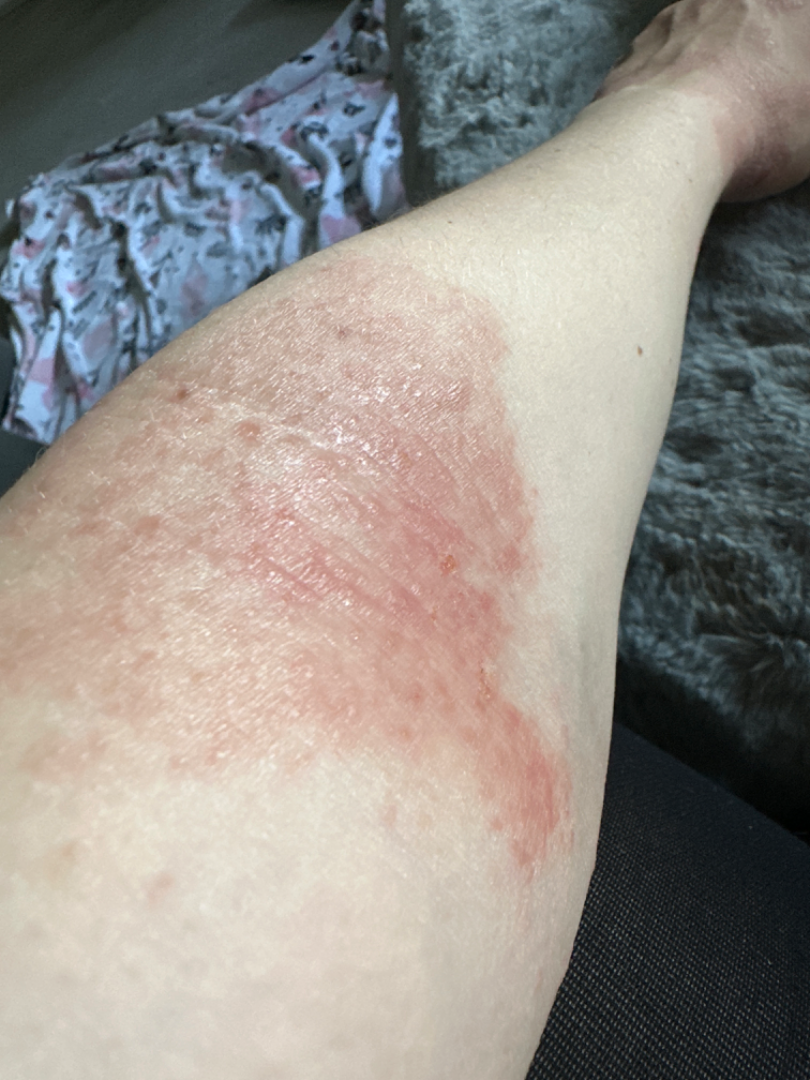| feature | finding |
|---|---|
| patient describes the issue as | a rash |
| described texture | raised or bumpy |
| location | arm |
| view | at an angle |
| symptom duration | more than one year |
| subject | female, age 30–39 |
| reported symptoms | enlargement, bothersome appearance and itching |
| clinical impression | most consistent with Eczema; a more distant consideration is Tinea; lower on the differential is Allergic Contact Dermatitis |